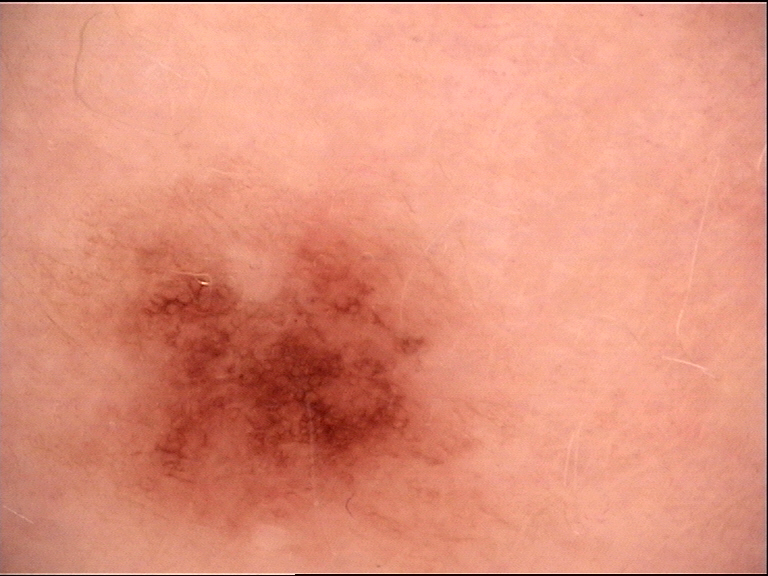Case: A dermoscopy image of a single skin lesion. Impression: The diagnostic label was a dysplastic junctional nevus.